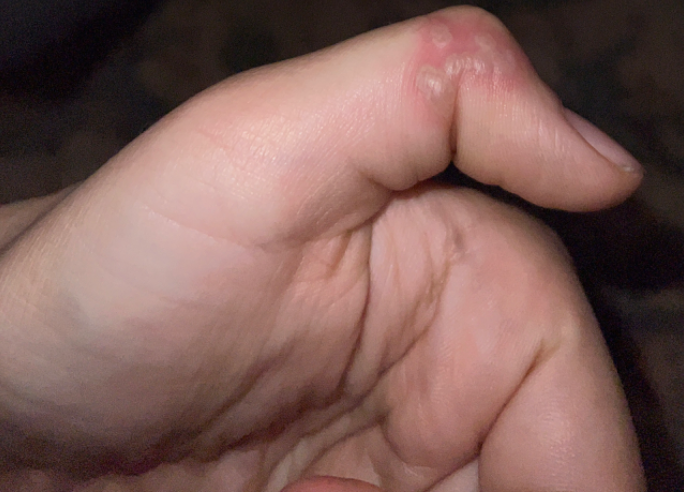| key | value |
|---|---|
| patient | female, age 18–29 |
| framing | close-up |
| impression | Herpes Simplex (1.00) |